An image taken at a distance:
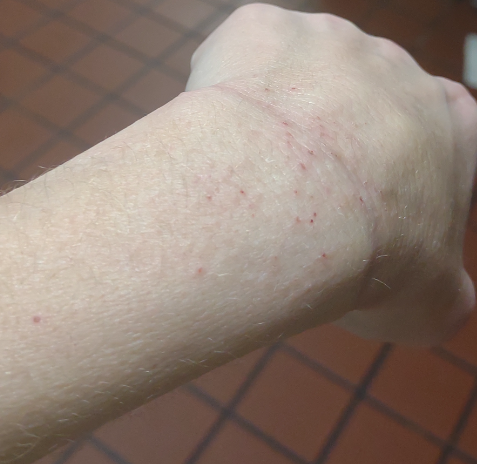The skin findings could not be characterized from the image.